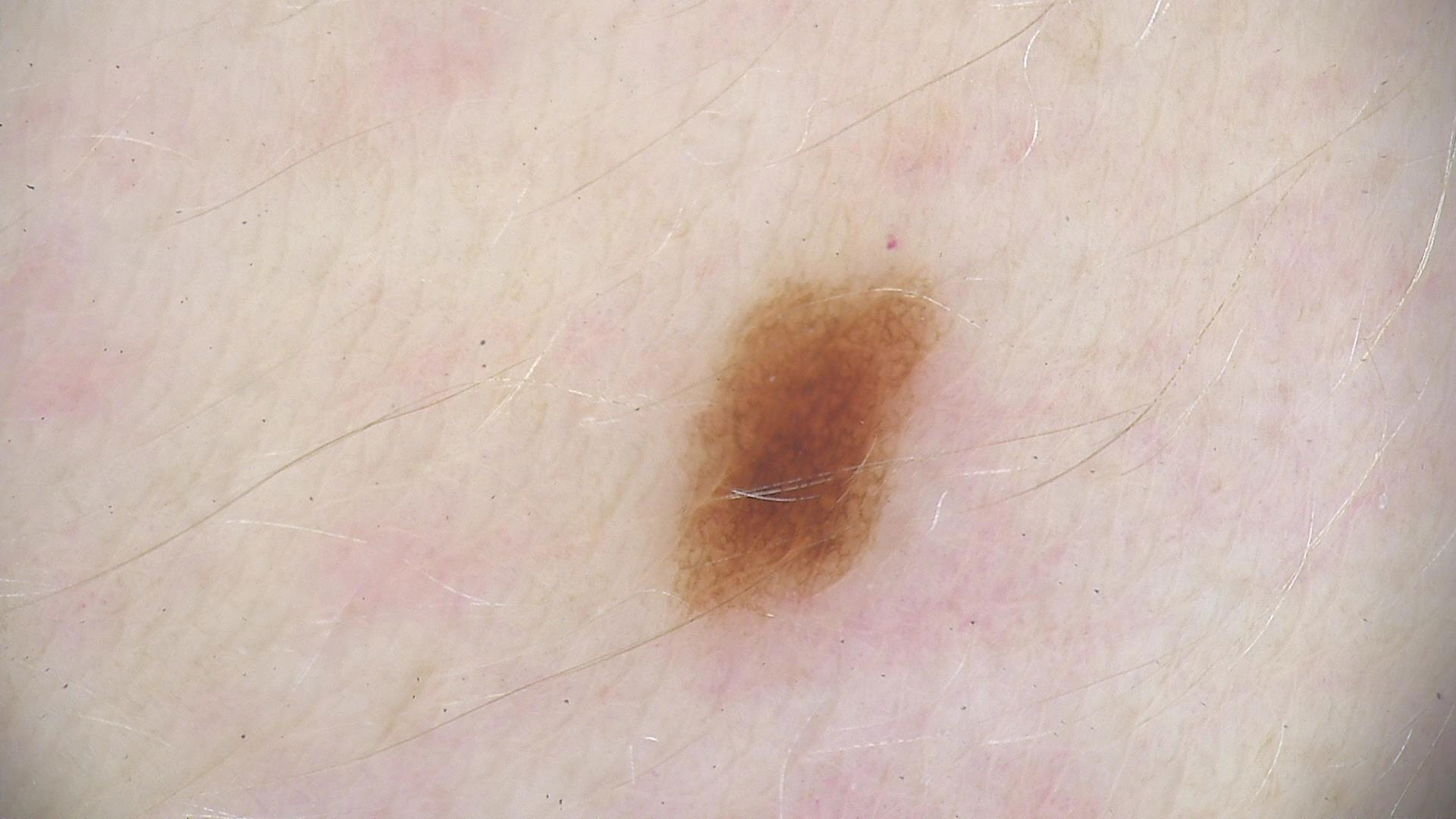image type = dermoscopy
label = dysplastic junctional nevus (expert consensus)